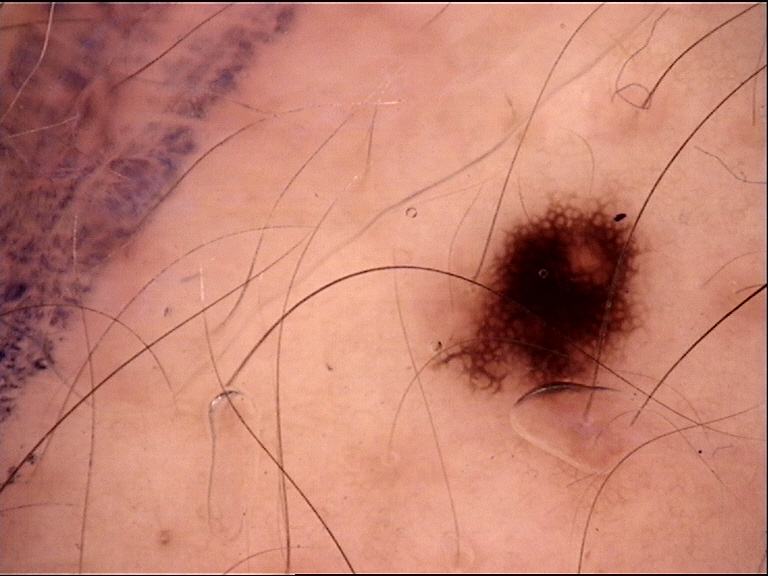{
  "image": "dermoscopy",
  "diagnosis": {
    "name": "junctional nevus",
    "code": "jb",
    "malignancy": "benign",
    "super_class": "melanocytic",
    "confirmation": "expert consensus"
  }
}